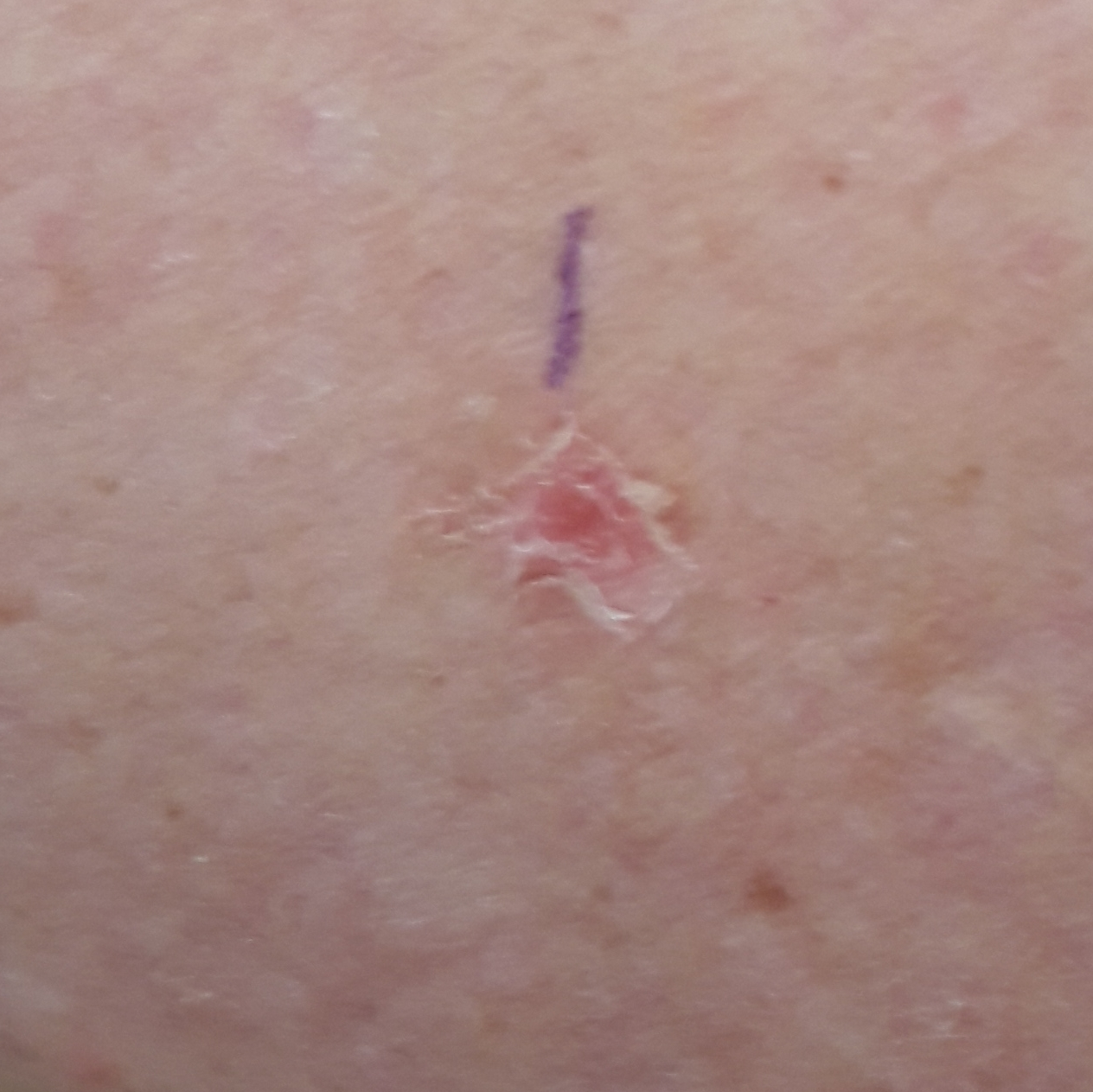| feature | finding |
|---|---|
| imaging | clinical photograph |
| anatomic site | a thigh |
| symptoms | elevation / no itching |
| impression | actinic keratosis (clinical consensus) |